The affected area is the front of the torso, leg and back of the torso; this is a close-up image — 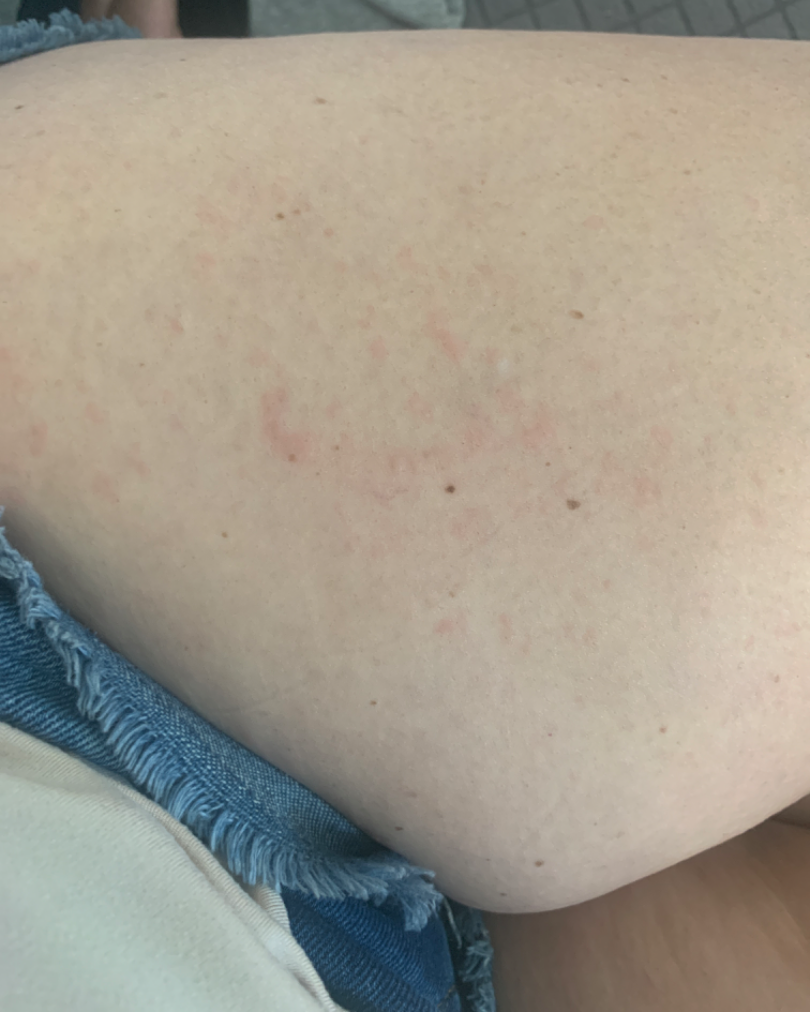Q: Could the case be diagnosed?
A: could not be assessed